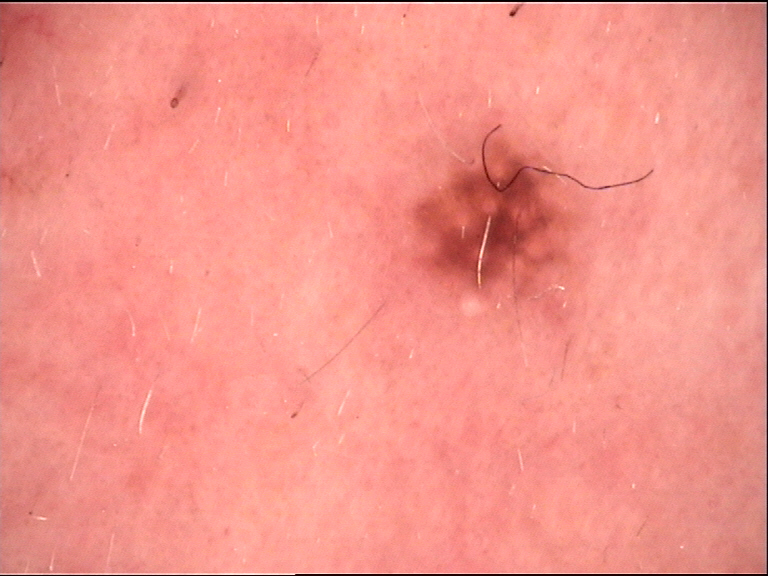<case>
<diagnosis>
<name>Miescher nevus</name>
<code>mcb</code>
<malignancy>benign</malignancy>
<super_class>melanocytic</super_class>
<confirmation>expert consensus</confirmation>
</diagnosis>
</case>